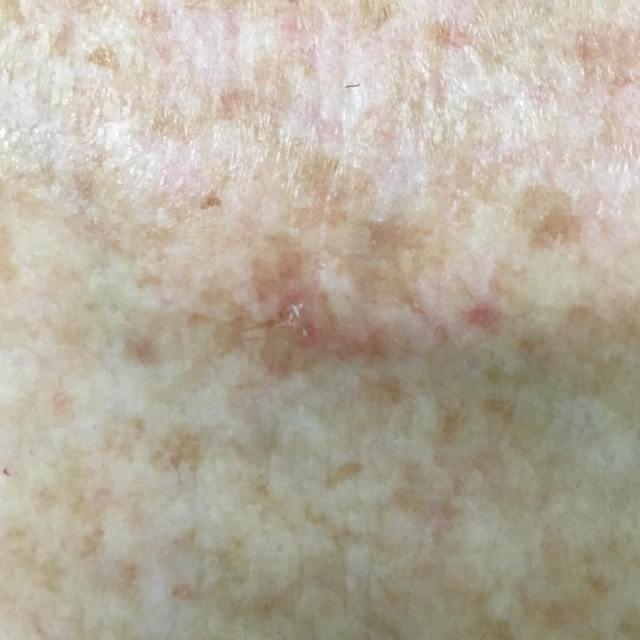A patient in their 40s. Located on the chest. By the patient's account, the lesion itches, but has not grown and has not bled. Expert review favored an actinic keratosis.